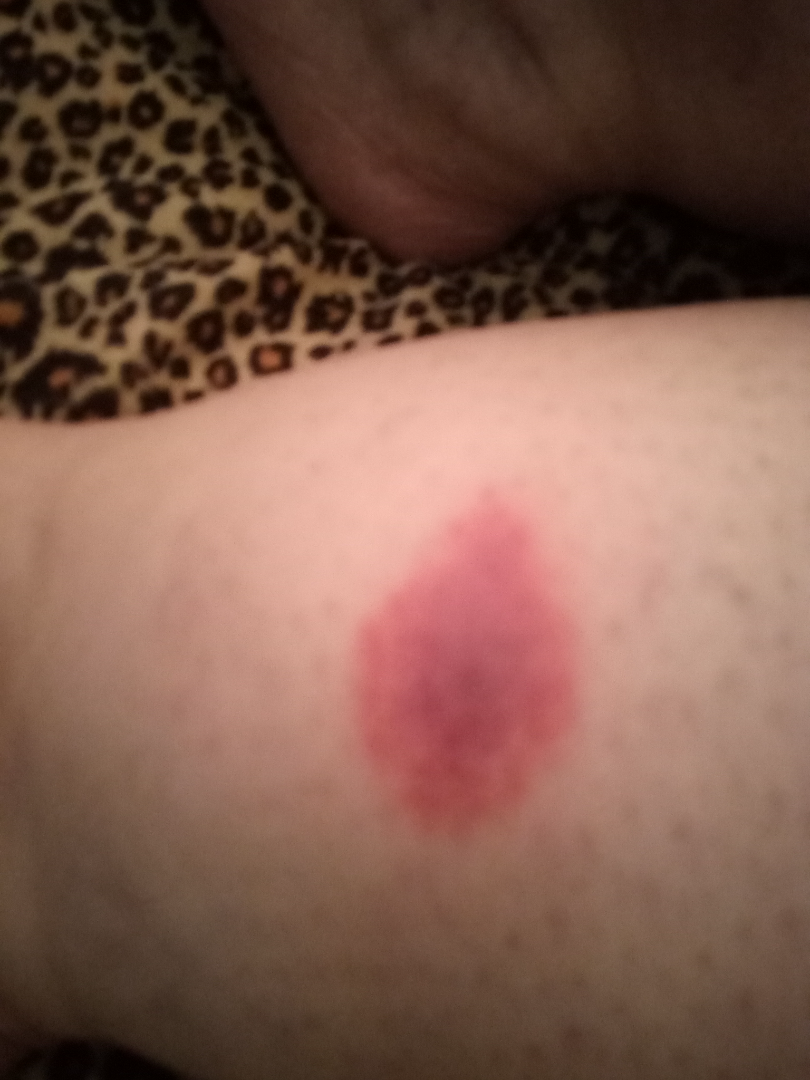Lay reviewers estimated Monk Skin Tone 2.
This is a close-up image.
No associated systemic symptoms reported.
The affected area is the leg.
The reviewing dermatologist's impression was: Insect Bite (leading); ecchymoses (possible).